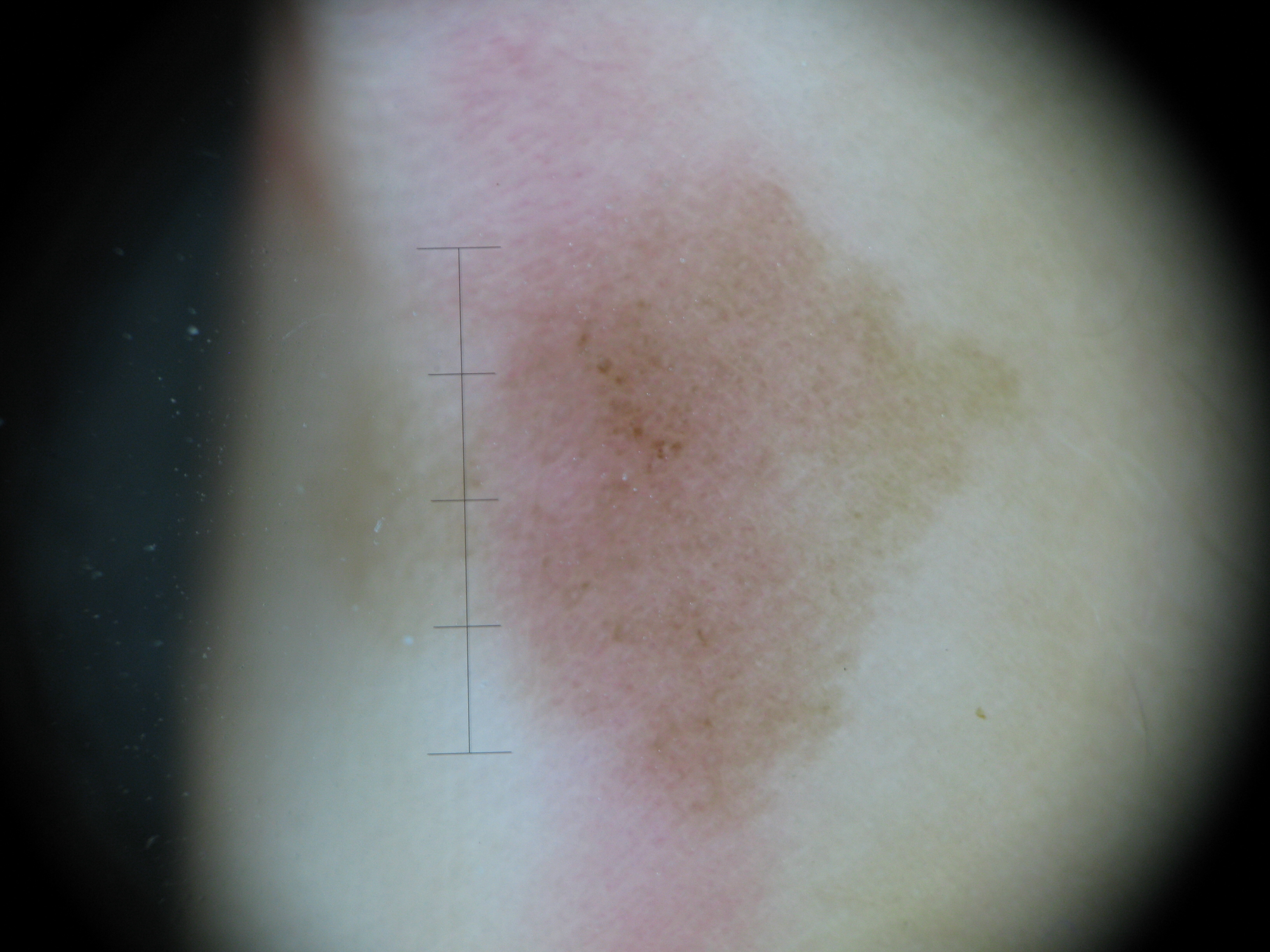Impression:
Diagnosed as a banal lesion — an acral junctional nevus.